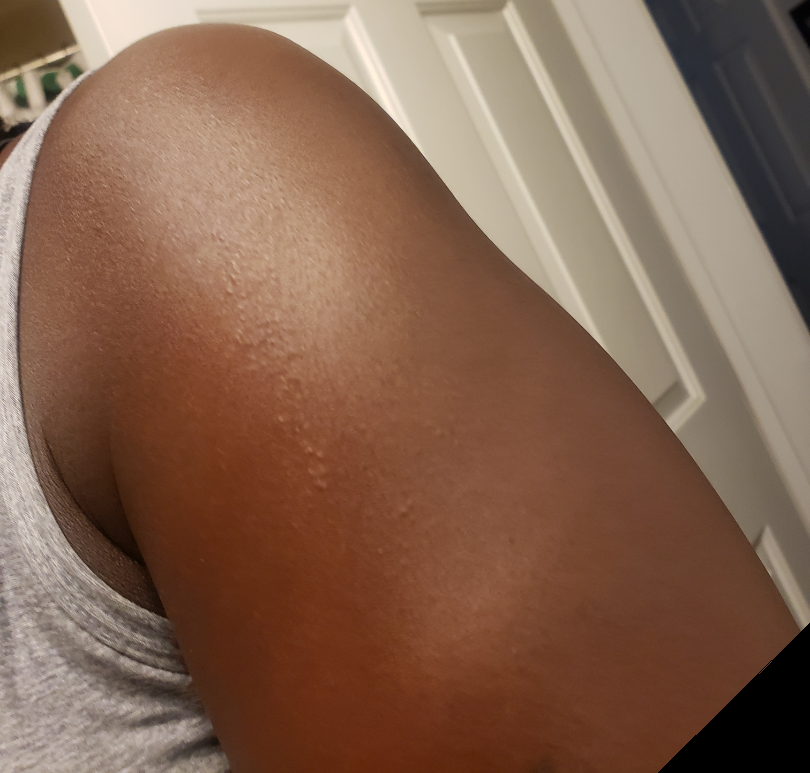view = at a distance; location = arm; diagnostic considerations = reviewed remotely by three dermatologists: Eczema and Lichen striatus were each considered, in no particular order.